A close-up photograph. The affected area is the leg and front of the torso. The contributor is 60–69, female:
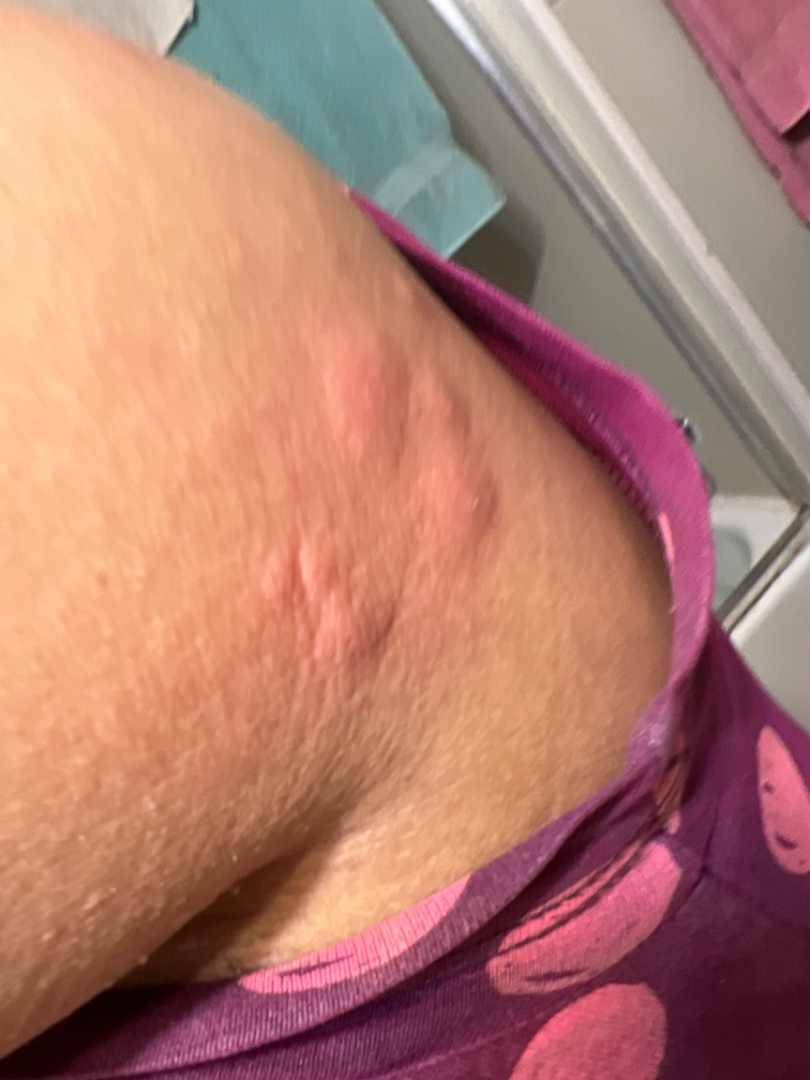| field | value |
|---|---|
| symptom duration | about one day |
| associated systemic symptoms | none reported |
| described texture | raised or bumpy |
| clinical impression | favoring Urticaria; possibly Insect Bite; less probable is Allergic Contact Dermatitis |